Female subject, age 30–39 · the back of the hand and top or side of the foot are involved · this image was taken at an angle.
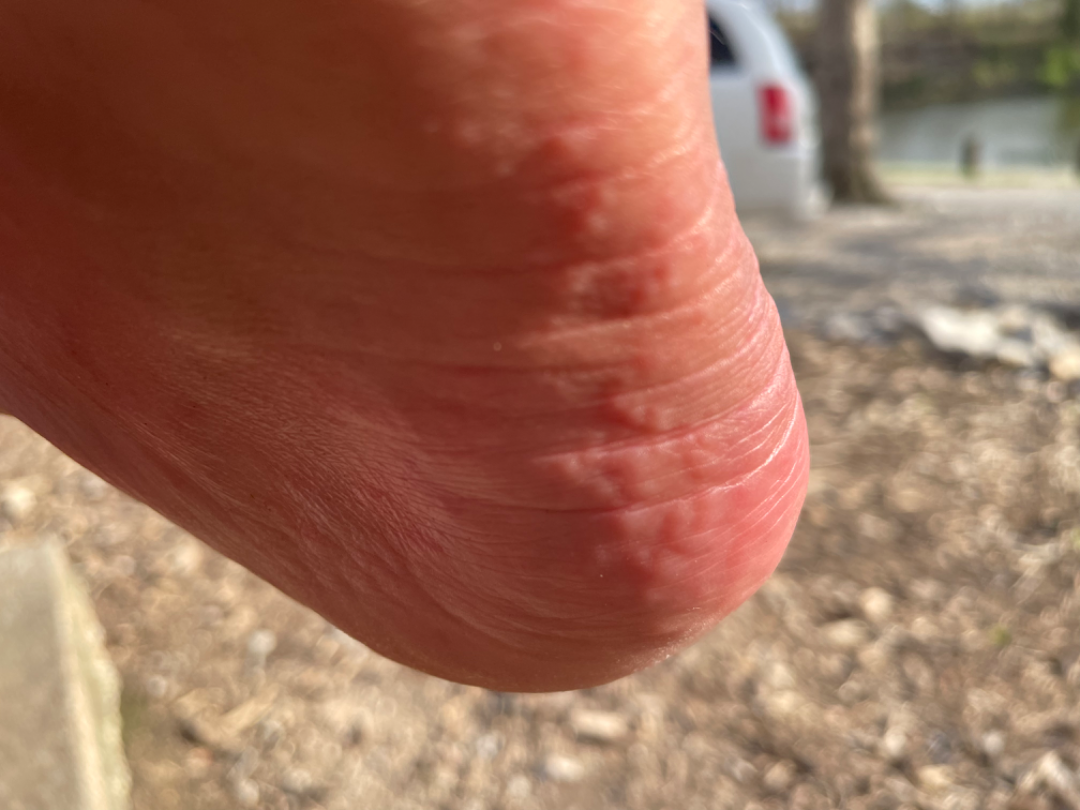The condition could not be reliably identified from the image.